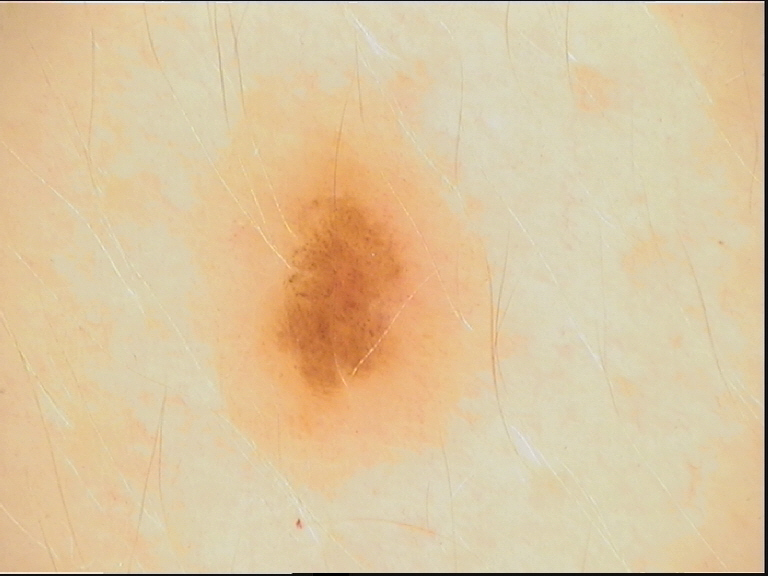image: dermatoscopy
diagnosis:
  name: dysplastic junctional nevus
  code: jd
  malignancy: benign
  super_class: melanocytic
  confirmation: expert consensus